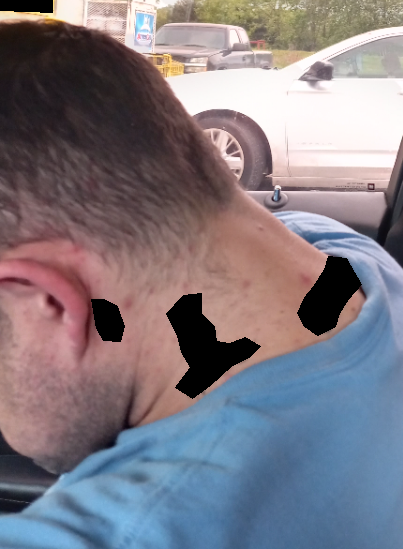Symptoms reported: burning, pain, bothersome appearance, enlargement and itching. The contributor is male. The patient notes the lesion is fluid-filled. The affected area is the head or neck. This image was taken at a distance. Favoring Acne; possibly Folliculitis; less probable is Acne keloidalis.